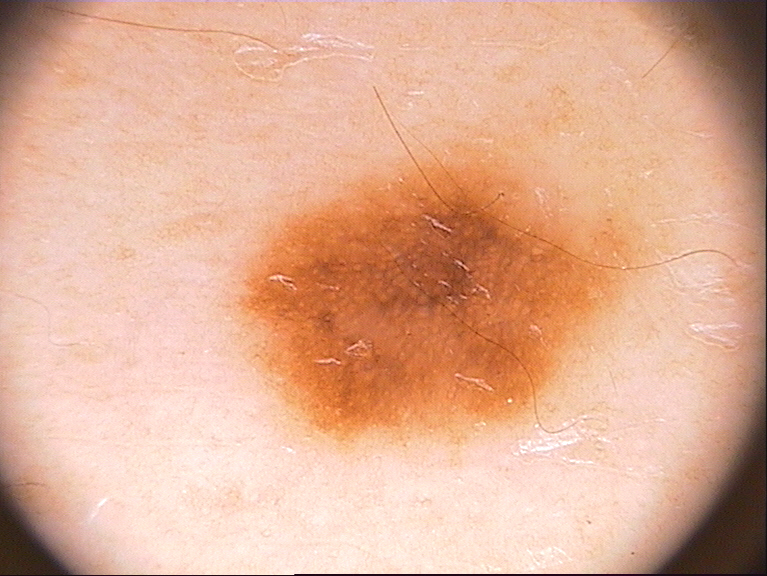{"patient": {"sex": "male", "age_approx": 60}, "image": {"modality": "dermoscopy"}, "lesion_location": {"bbox_xyxy": [223, 133, 652, 456]}, "dermoscopic_features": {"present": ["pigment network"], "absent": ["streaks", "milia-like cysts", "negative network", "globules"]}, "lesion_extent": "moderate", "diagnosis": {"name": "melanoma", "malignancy": "malignant", "lineage": "melanocytic", "provenance": "histopathology"}}